A clinical photo of a skin lesion taken with a smartphone. A male patient age 64. By history, prior skin cancer (patient or family), pesticide exposure, no prior malignancy (patient or family), and no tobacco use: 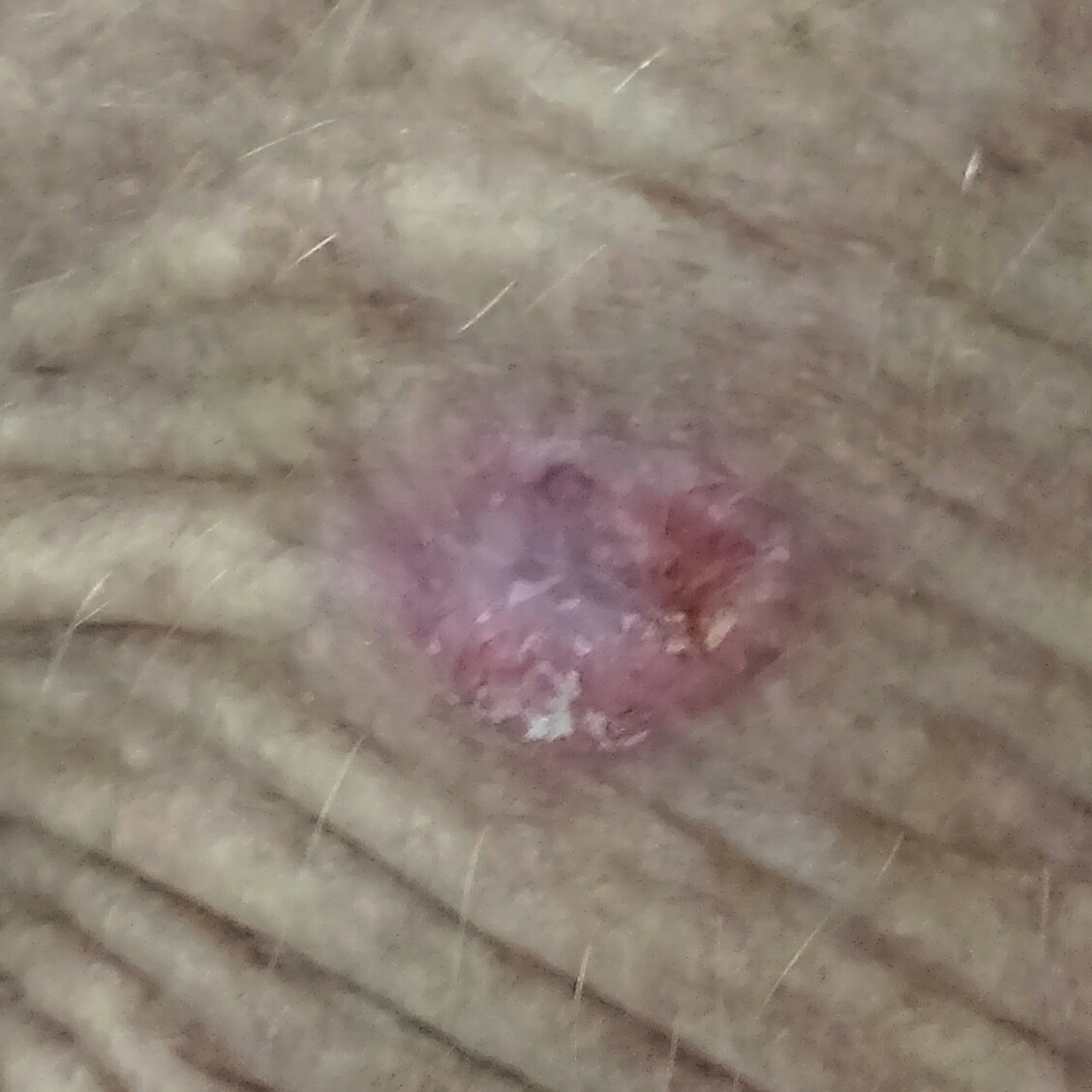site: a forearm; lesion size: 14x10 mm; symptoms: itching, bleeding, growth, elevation / no change in appearance; diagnosis: basal cell carcinoma (biopsy-proven).